A dermoscopic photograph of a skin lesion:
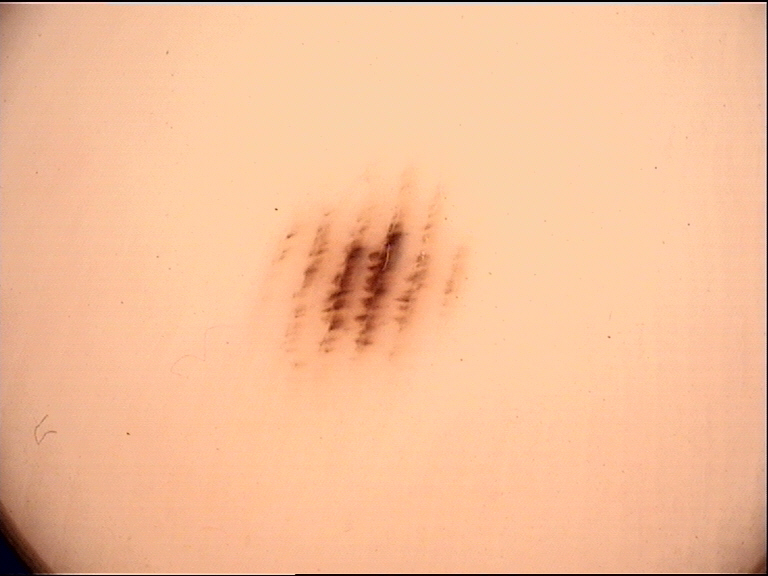Findings:
* lesion type: banal
* diagnostic label: acral junctional nevus (expert consensus)